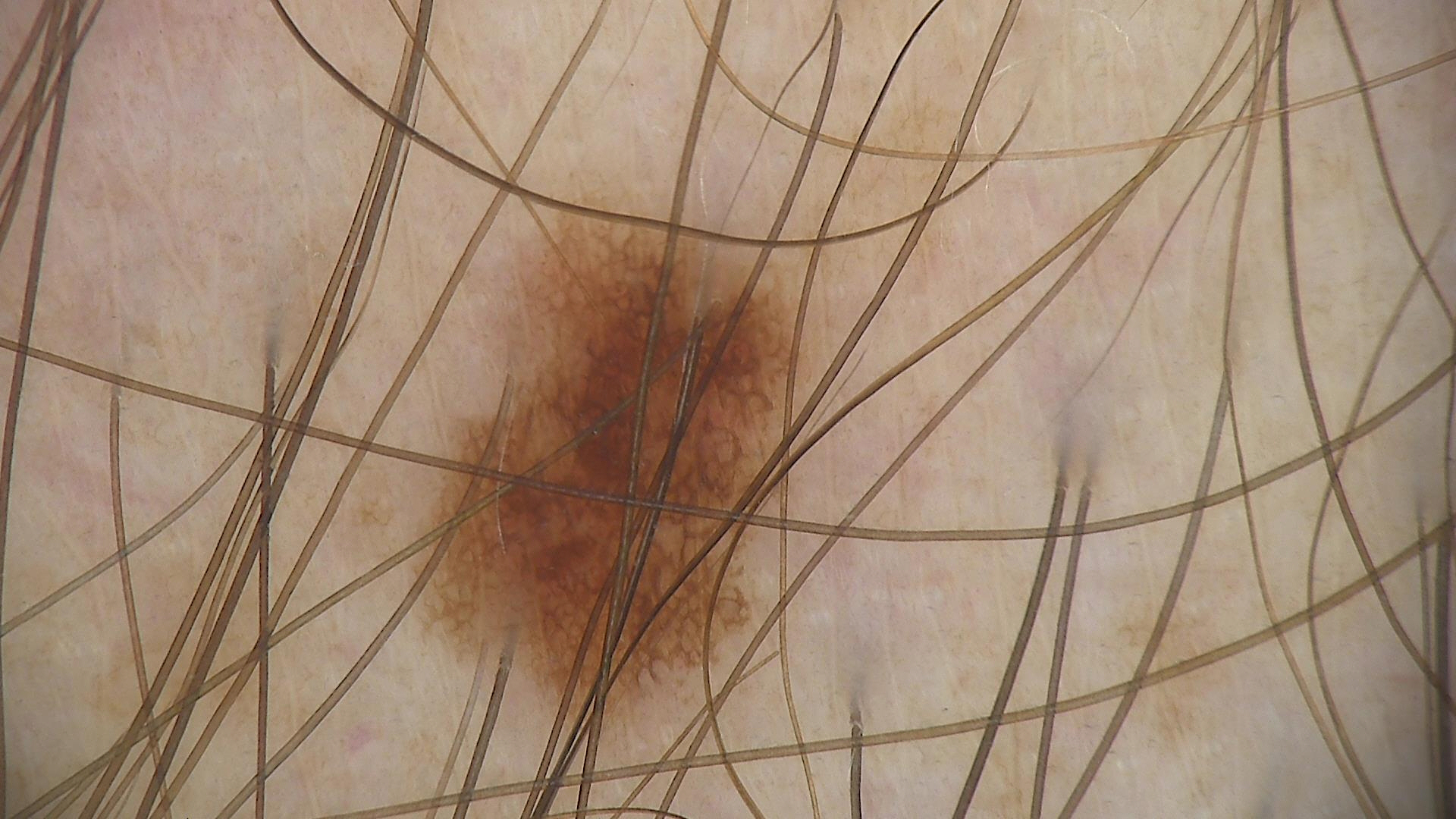The diagnostic label was a dysplastic junctional nevus.